This image was taken at an angle · the patient is female · the affected area is the front of the torso:
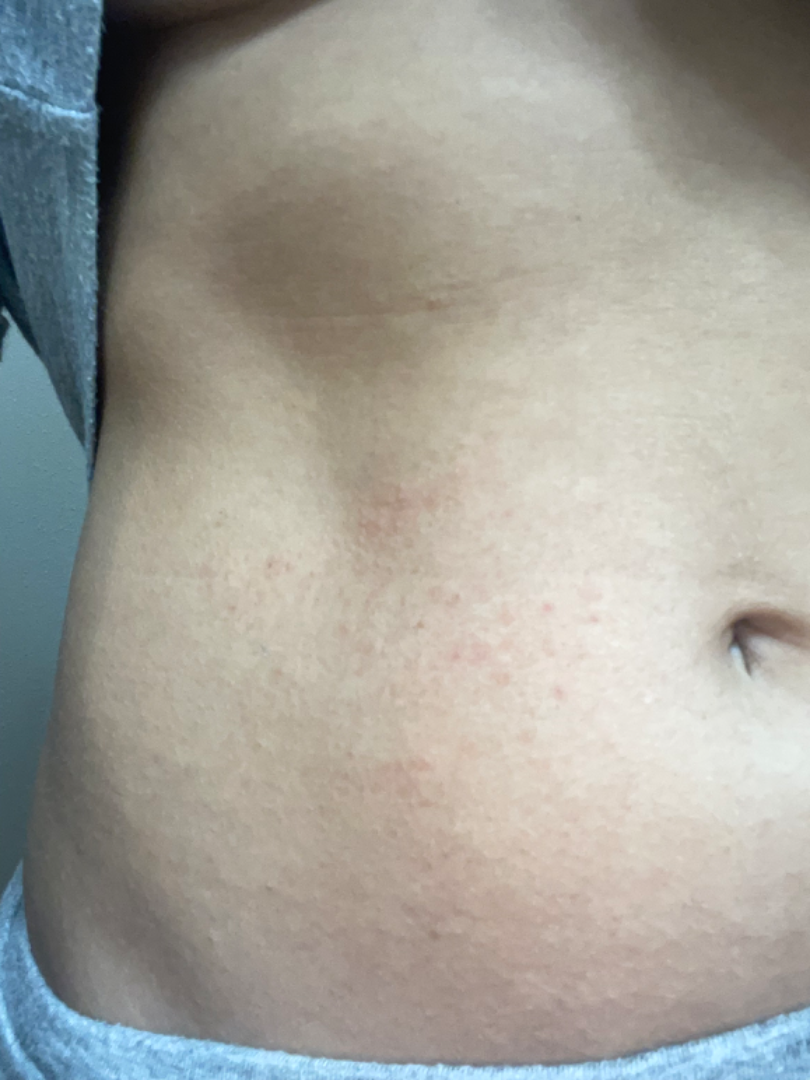assessment: indeterminate from the photograph